A clinical photograph of a skin lesion; the patient is FST II; a male subject in their 70s: 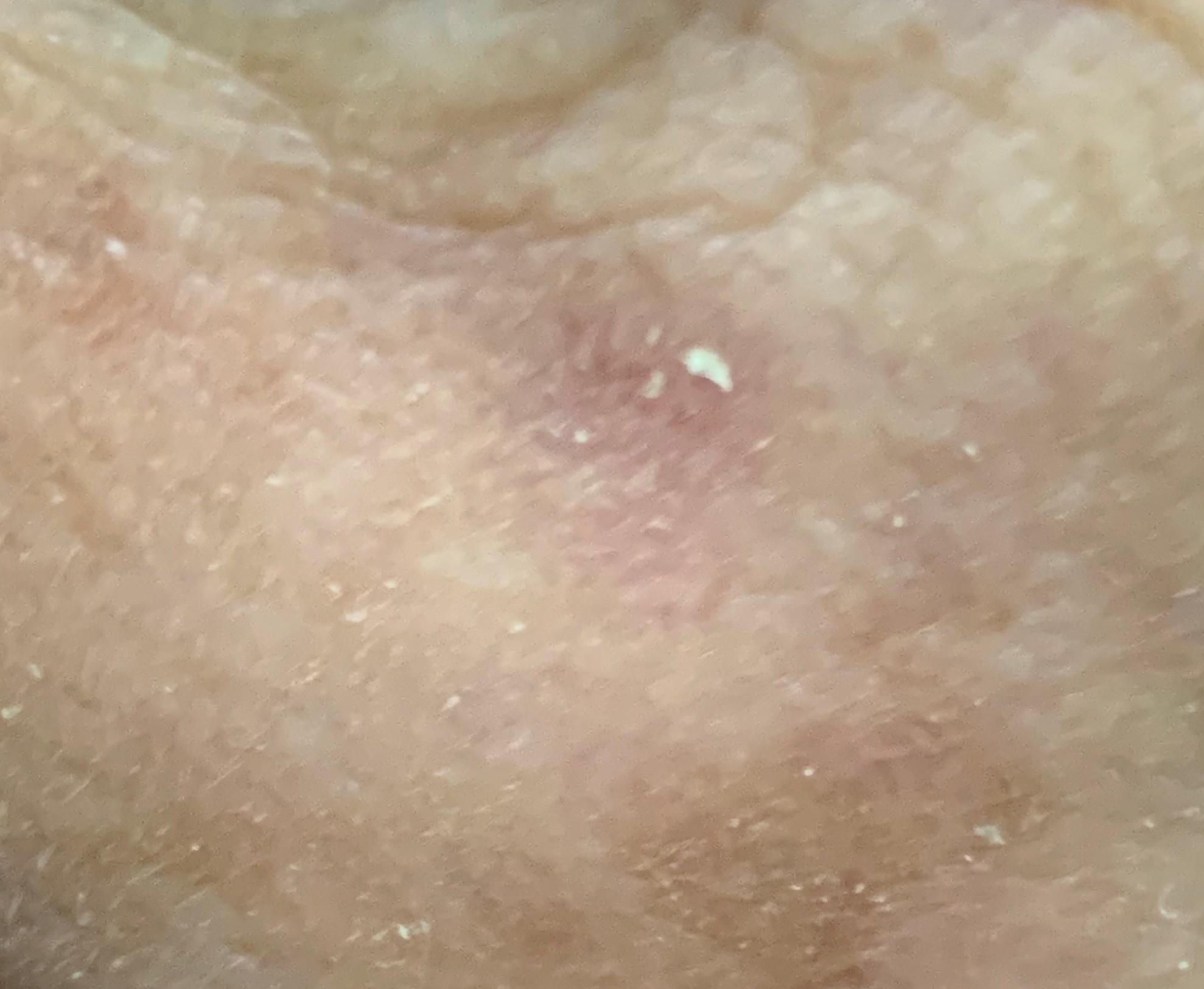The lesion involves the head or neck. The diagnostic impression was a lesion with uncertain malignant potential — a solar or actinic keratosis.